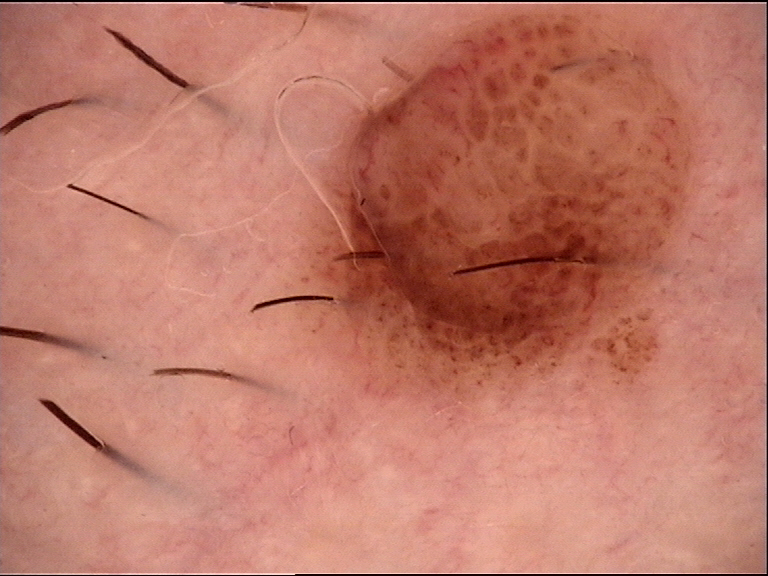Diagnosed as a compound nevus.